A dermoscopic photograph of a skin lesion; a female patient in their 70s — 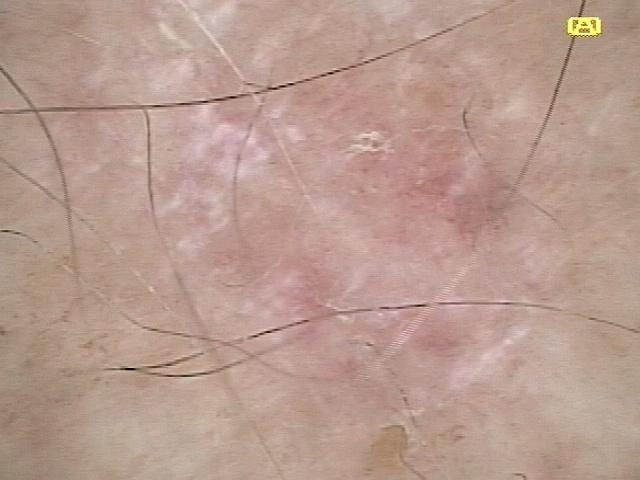{
  "lesion_location": {
    "region": "an upper extremity"
  },
  "diagnosis": {
    "name": "Squamous cell carcinoma",
    "malignancy": "malignant",
    "confirmation": "histopathology",
    "lineage": "epidermal"
  }
}